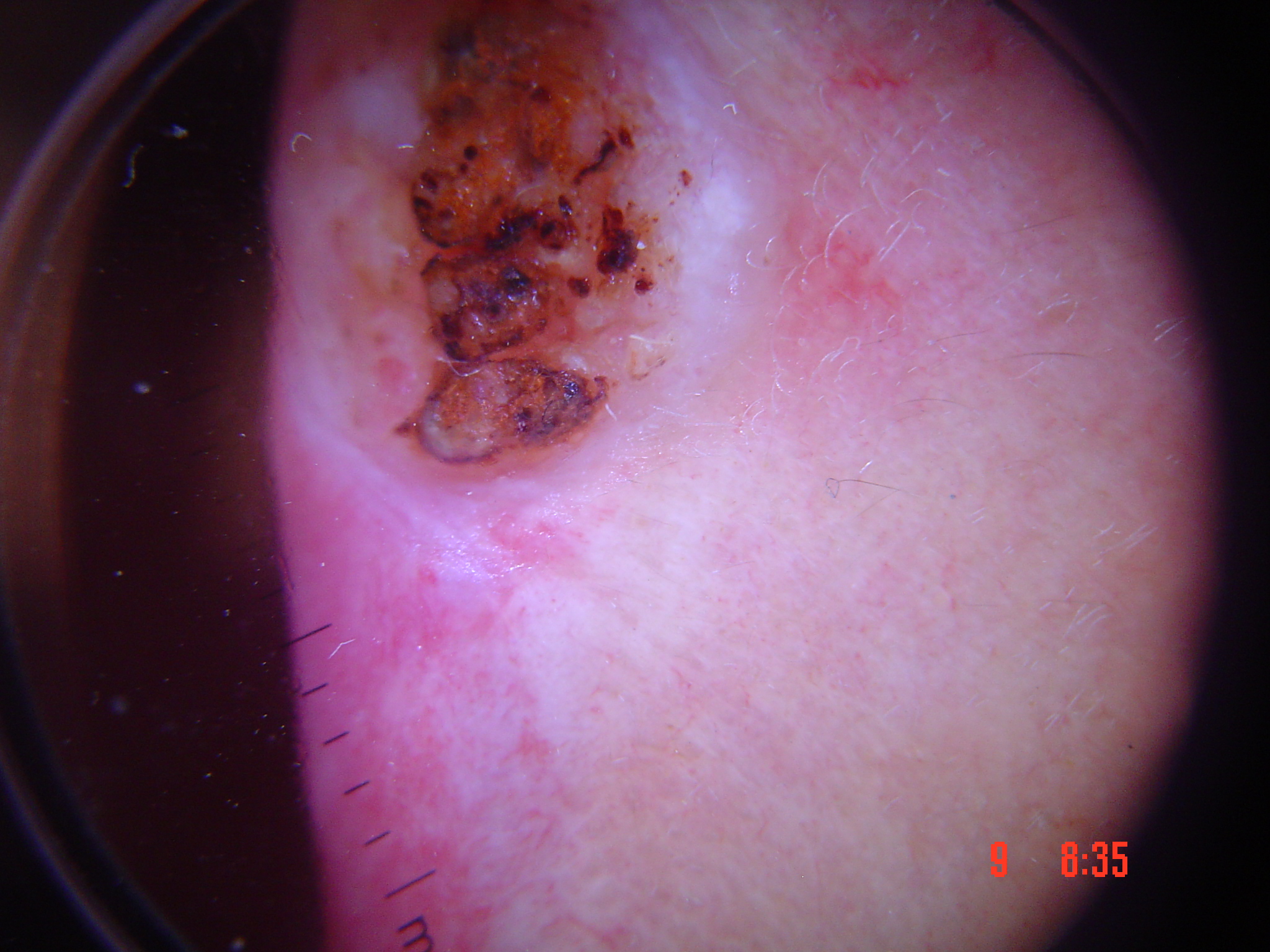The biopsy diagnosis was a squamous cell carcinoma.